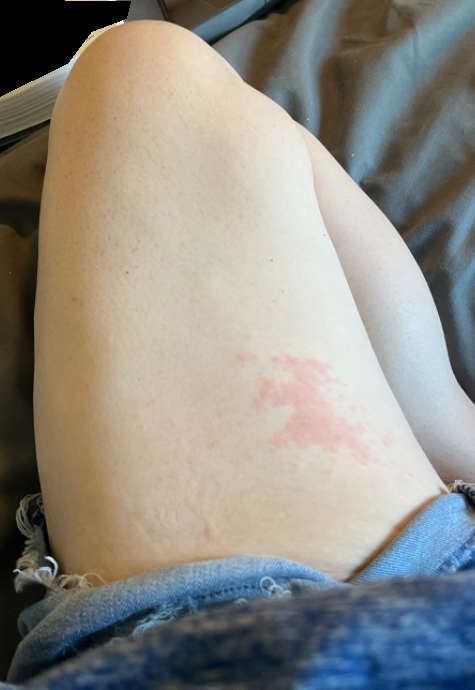image framing=at a distance; clinical impression=Acute dermatitis, NOS and Irritant Contact Dermatitis were considered with similar weight.